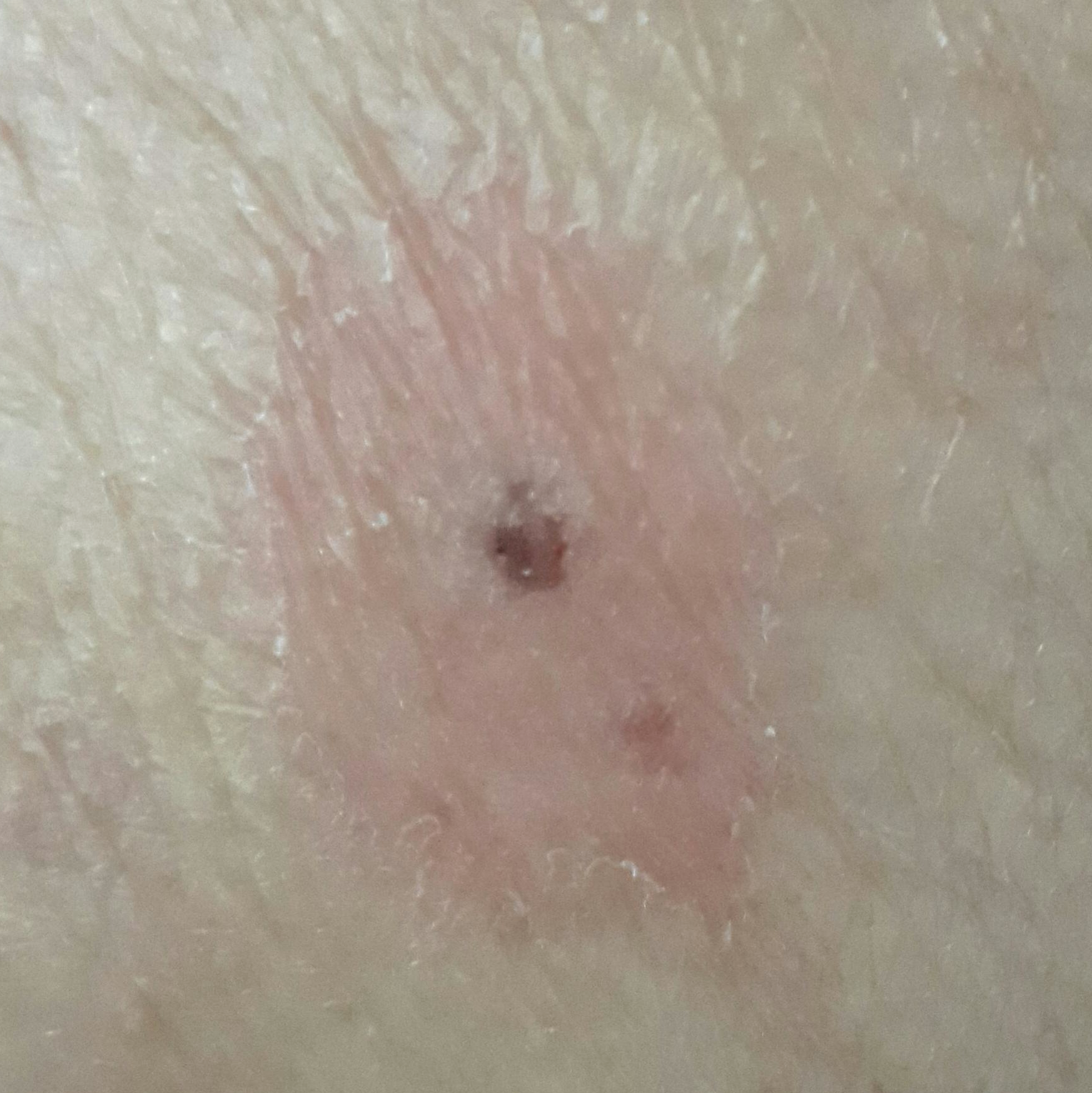Notes:
- image — clinical photograph
- subject — in their mid-40s
- patient-reported symptoms — change in appearance / no growth
- impression — nevus (clinical consensus)